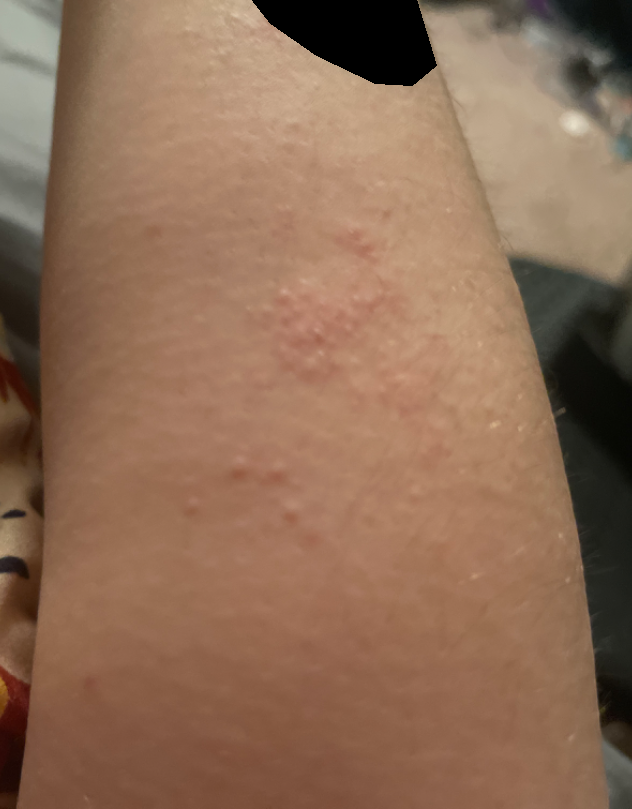<summary>
<assessment>unable to determine</assessment>
<shot_type>close-up</shot_type>
<skin_tone>
  <fitzpatrick>III</fitzpatrick>
  <monk_skin_tone>2, 3</monk_skin_tone>
</skin_tone>
</summary>